A close-up photograph · the patient notes the condition has been present for less than one week · located on the arm · texture is reported as raised or bumpy and rough or flaky: 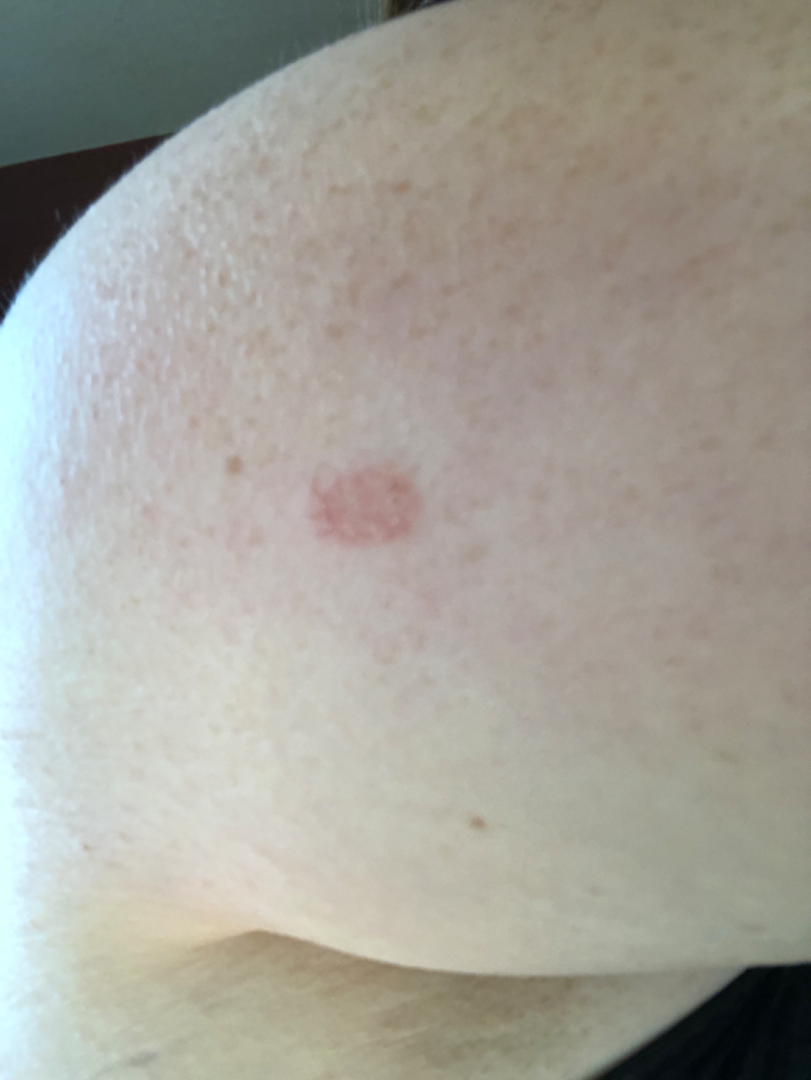Case summary:
- assessment · unable to determine